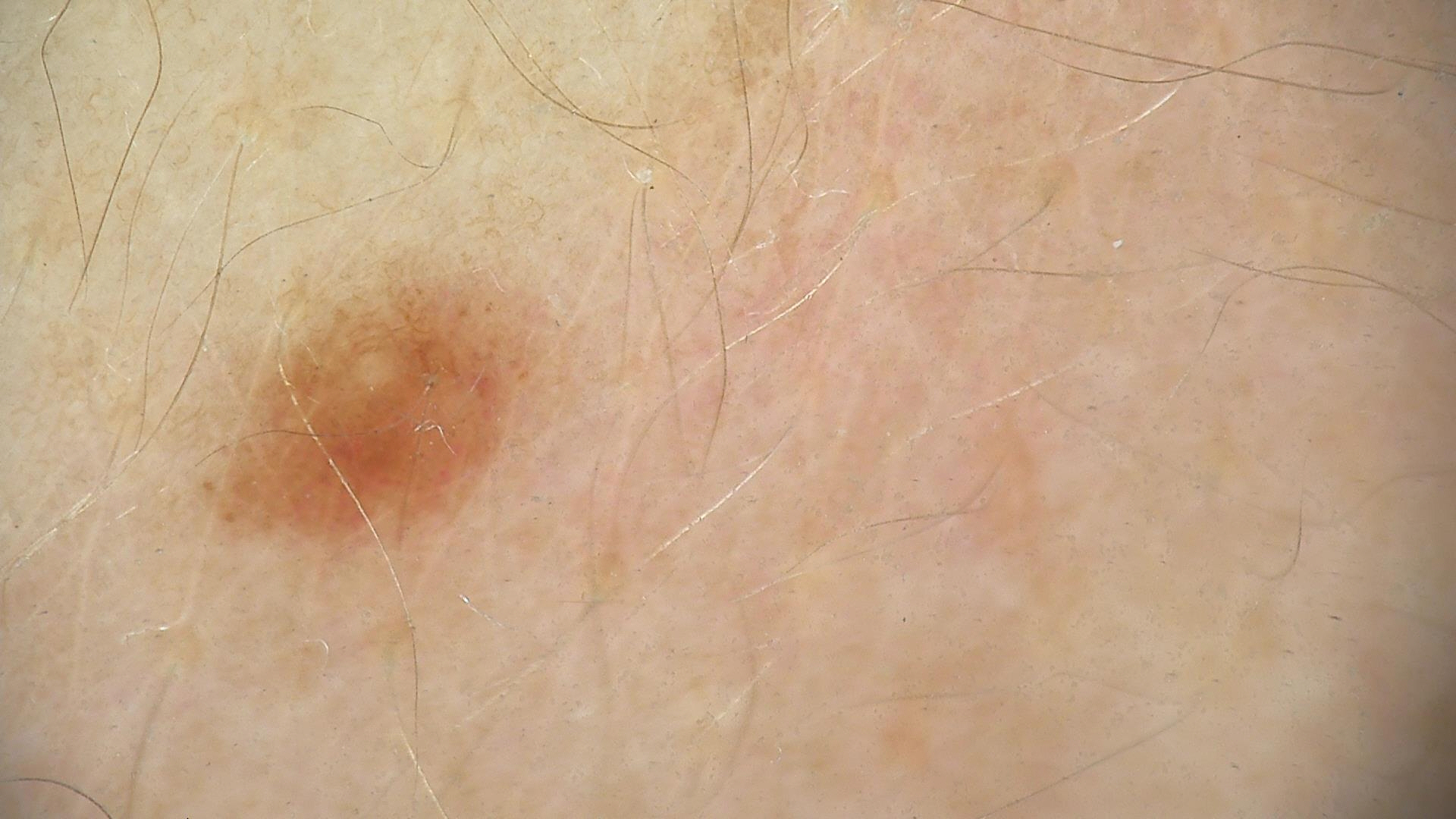Conclusion: Labeled as a dysplastic junctional nevus.